A skin lesion imaged with a dermatoscope — 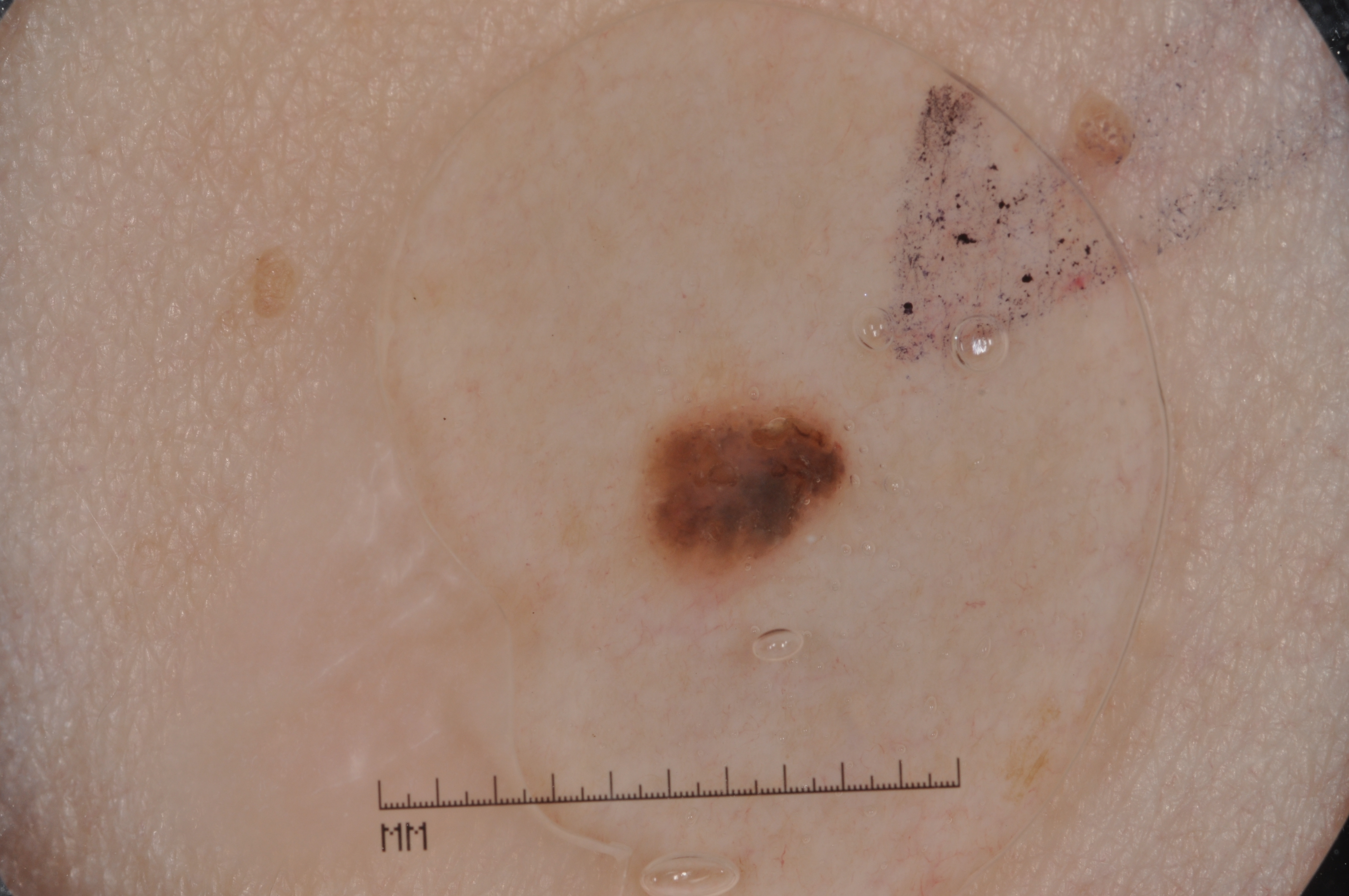As (left, top, right, bottom), the lesion is bounded by bbox(643, 385, 854, 588). The lesion is small relative to the field of view. Dermoscopic assessment notes milia-like cysts, with no streaks, negative network, or pigment network. Clinically diagnosed as a seborrheic keratosis, a benign skin lesion.